This image was taken at an angle. The affected area is the leg:
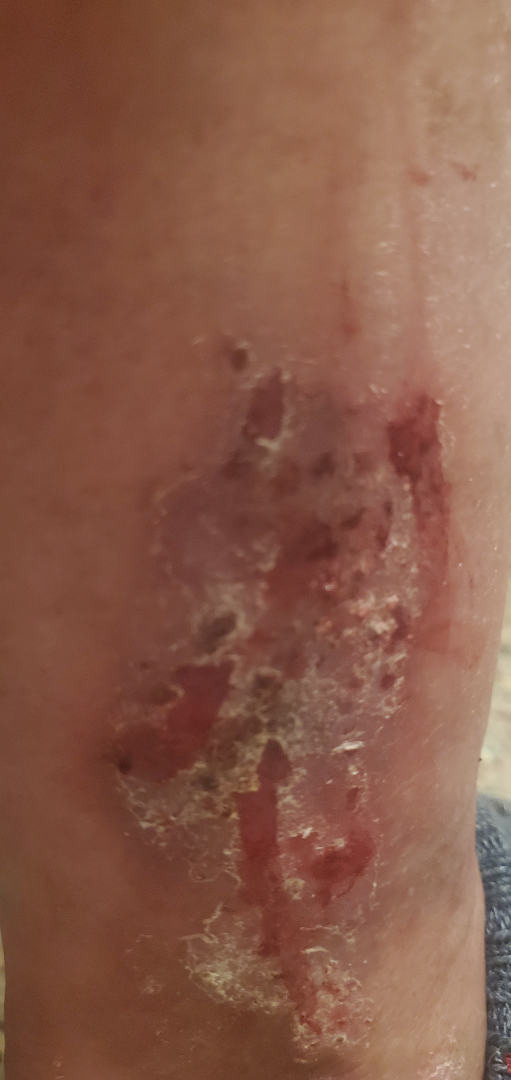- assessment — unable to determine